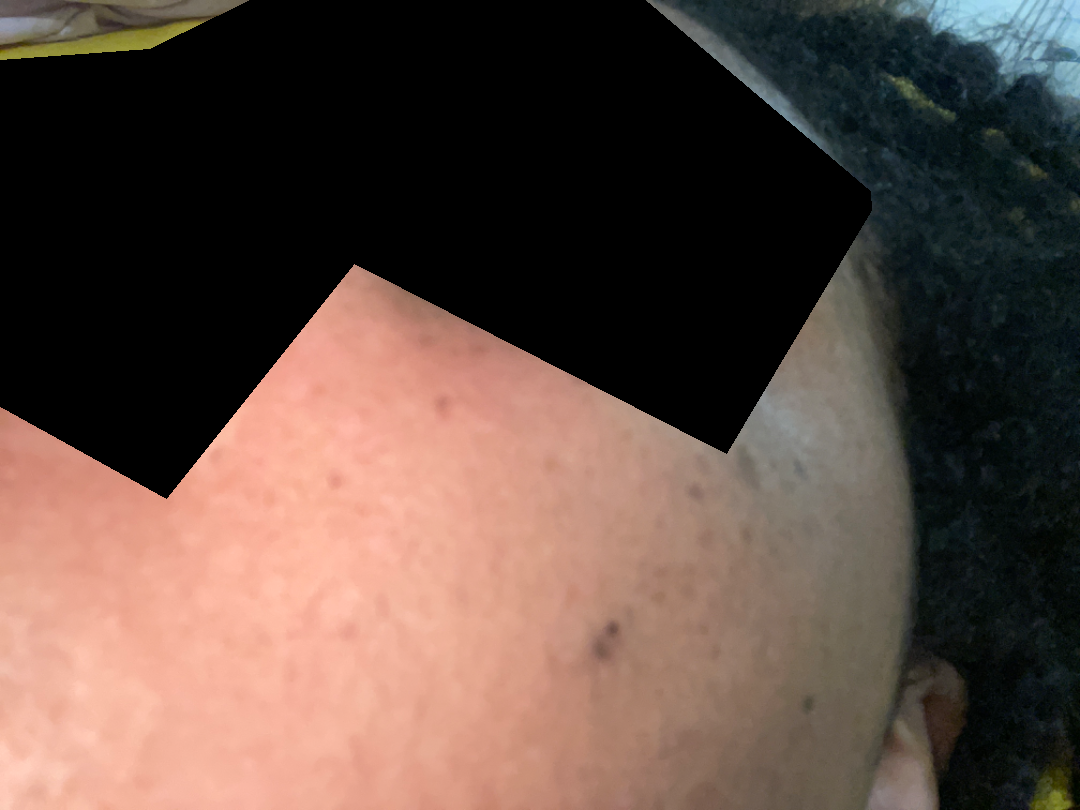No clear dermatological pathology was apparent in the photograph.
The patient described the issue as a rash.
The photo was captured at an angle.
Reported lesion symptoms include pain, bothersome appearance and itching.
Associated systemic symptoms include fatigue.
The head or neck is involved.
Reported duration is less than one week.